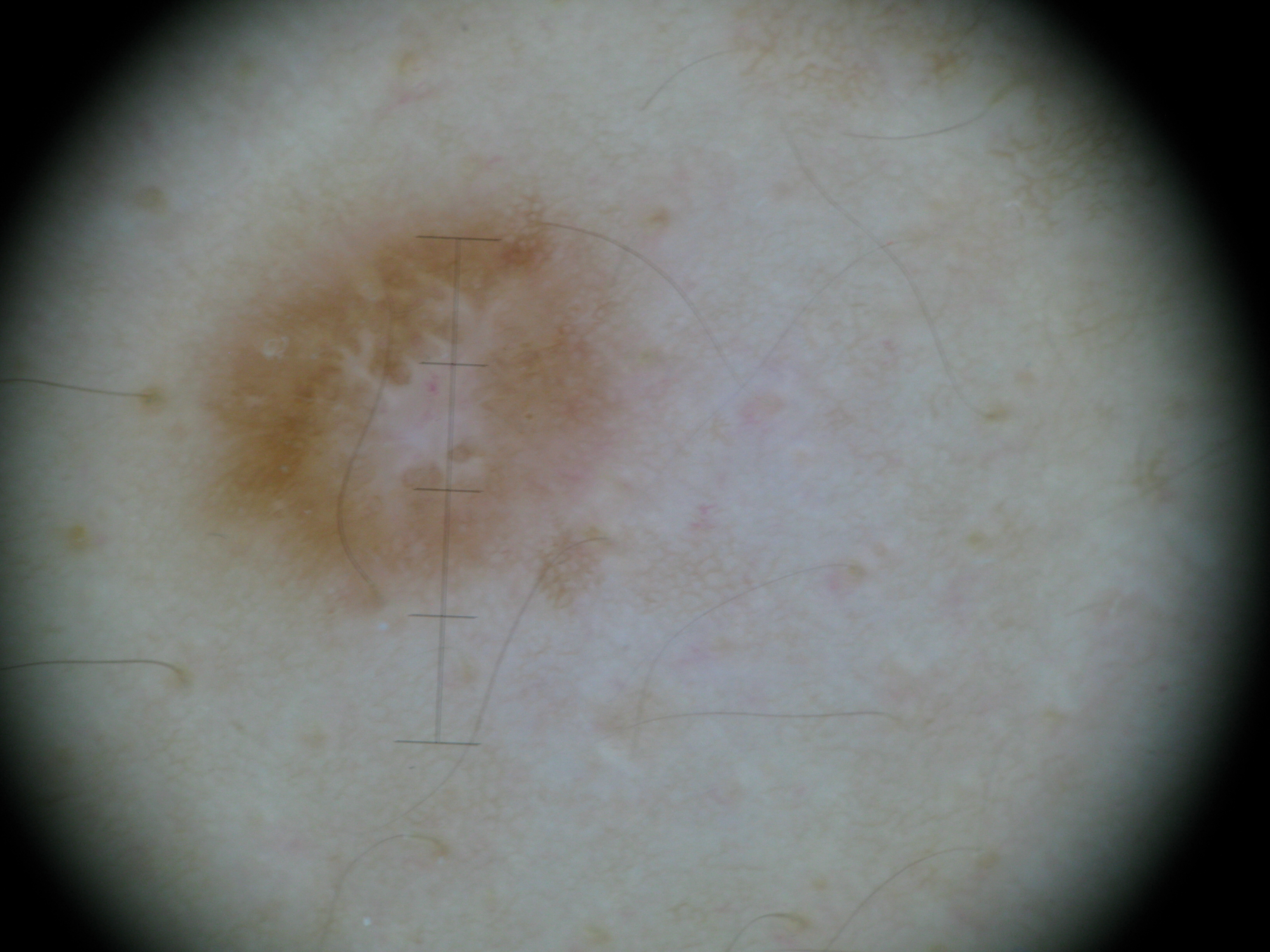Q: What kind of image is this?
A: dermatoscopy
Q: What is this lesion?
A: dermatofibroma (expert consensus)